A male subject aged 68 to 72. A skin lesion imaged with a dermatoscope: 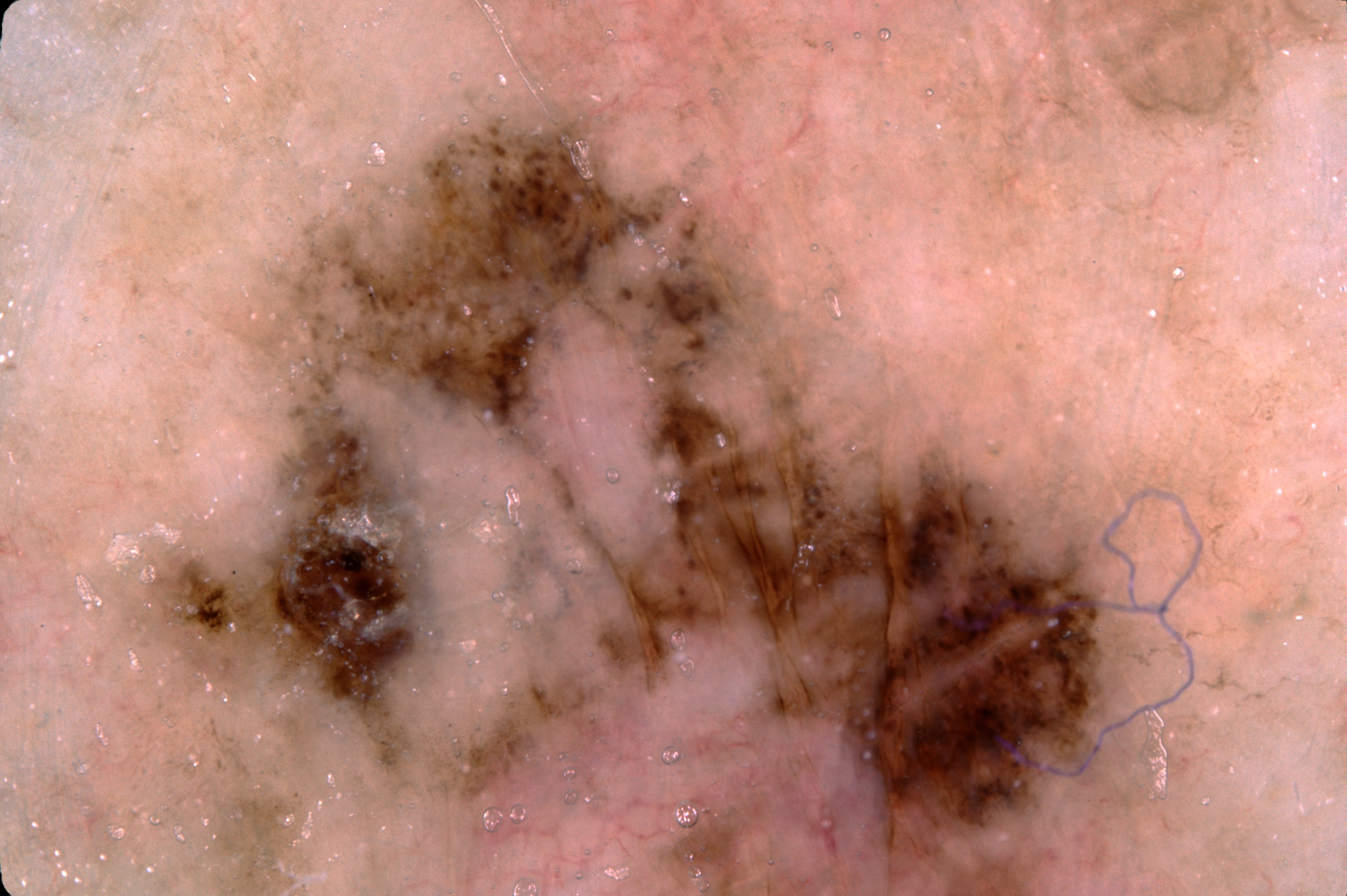With coordinates (x1, y1, x2, y2), the lesion spans [74,79,1123,894].
The lesion takes up a large portion of the image.
On dermoscopy, the lesion shows no negative network, milia-like cysts, streaks, or pigment network.
The biopsy diagnosis was a melanoma, a malignancy.